Dermoscopy of a skin lesion.
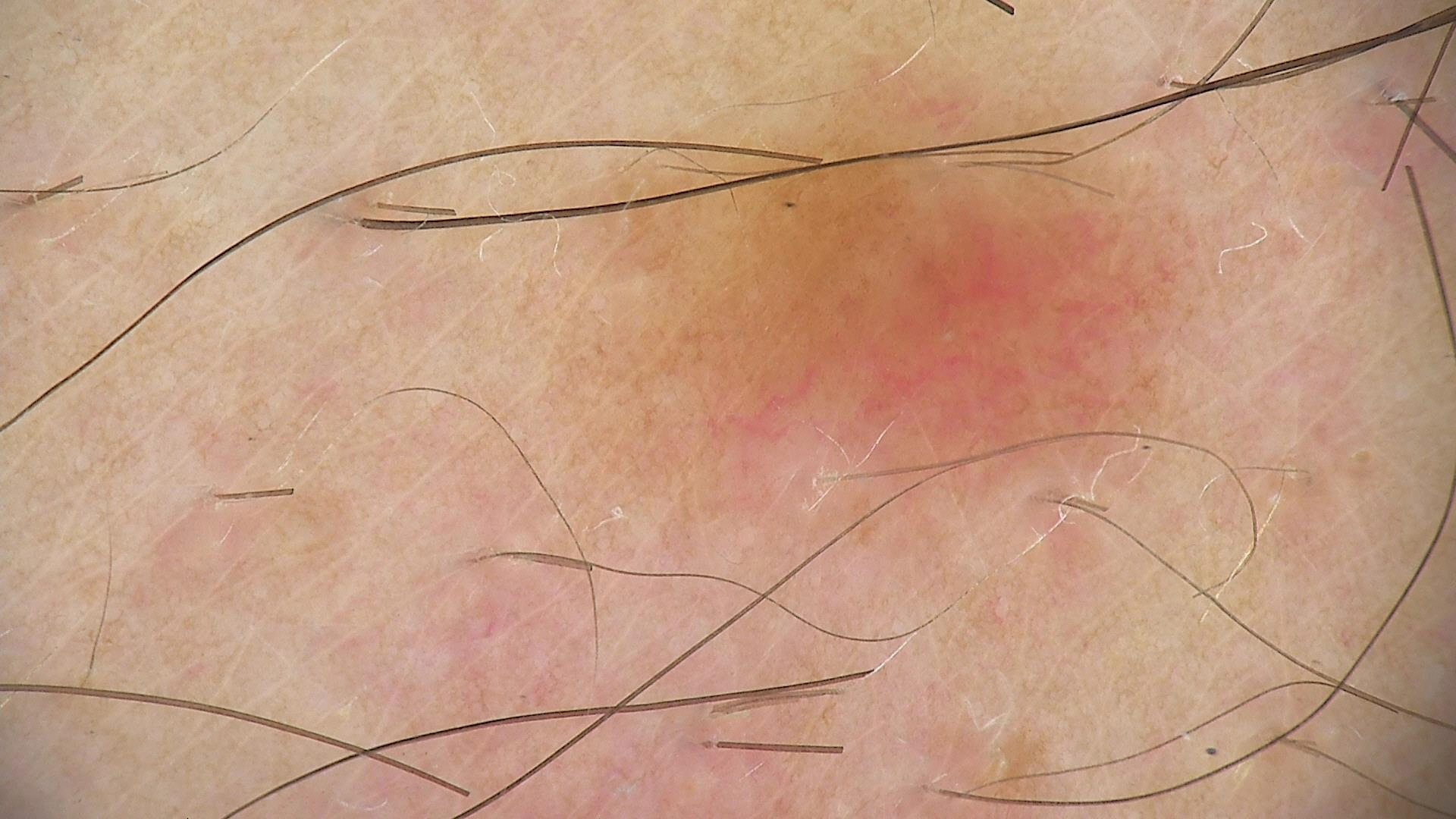{
  "diagnosis": {
    "name": "dysplastic junctional nevus",
    "code": "jd",
    "malignancy": "benign",
    "super_class": "melanocytic",
    "confirmation": "expert consensus"
  }
}